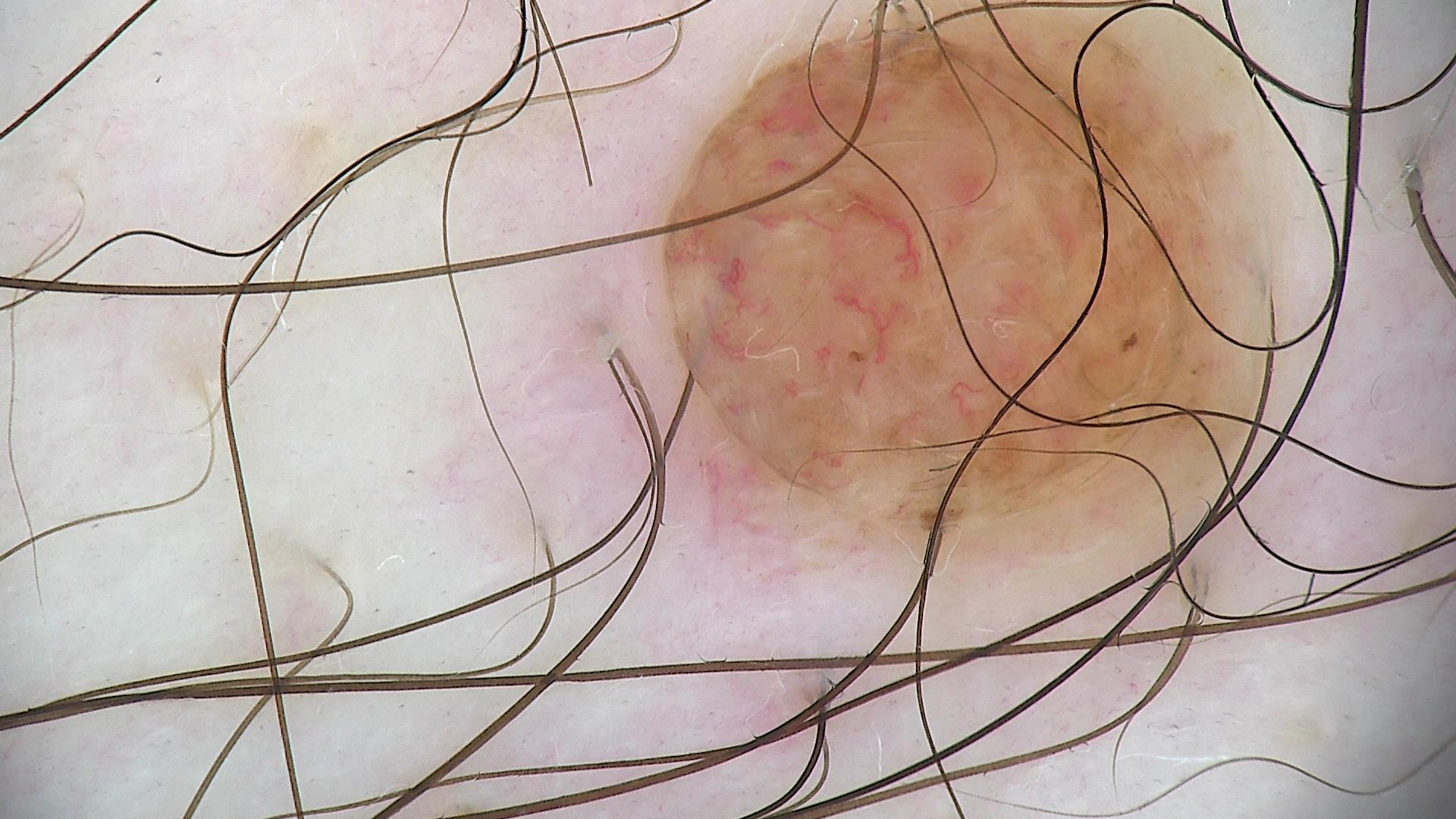Impression:
Consistent with a dermal nevus.